Female subject, age 70–79; this image was taken at an angle; located on the leg; the patient described the issue as a rash; texture is reported as raised or bumpy; no relevant systemic symptoms; the condition has been present for less than one week: 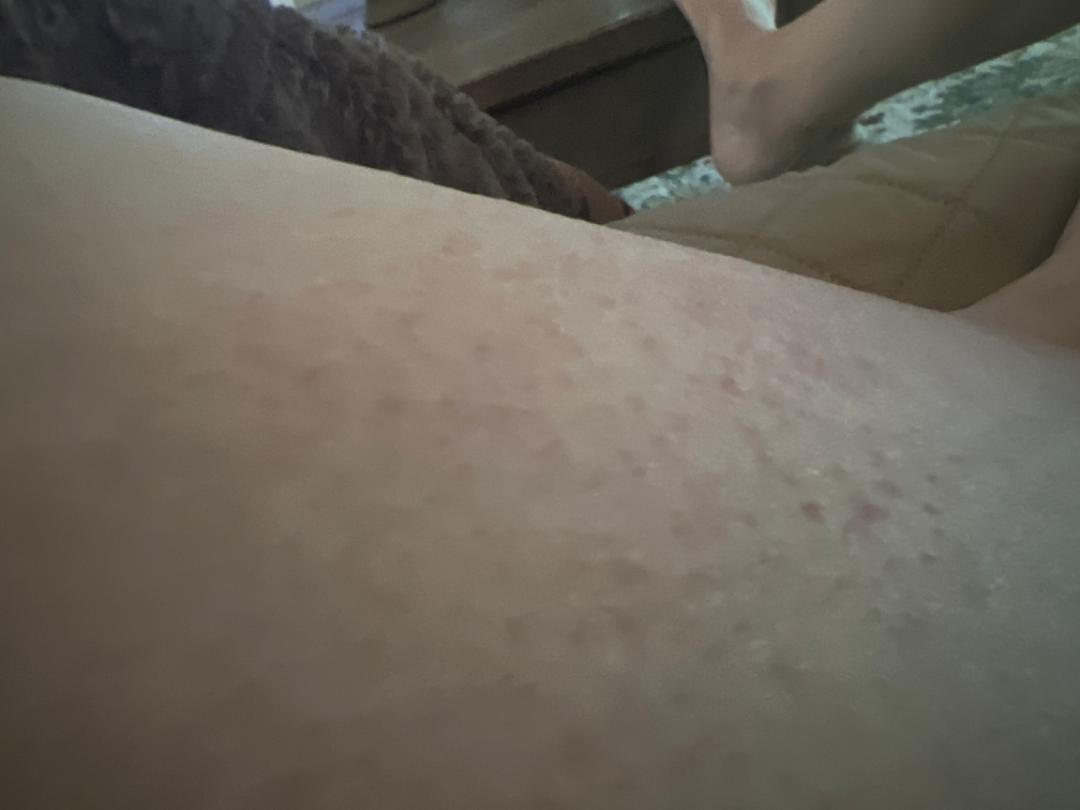assessment = three independent reviewers: the primary impression is Eczema; possibly Allergic Contact Dermatitis